The lesion is described as raised or bumpy and fluid-filled. The photo was captured at an angle. Fitzpatrick skin type V. The patient considered this a rash. Reported duration is about one day. The top or side of the foot, back of the hand, arm, sole of the foot and palm are involved. The lesion is associated with enlargement, pain, bothersome appearance and itching:
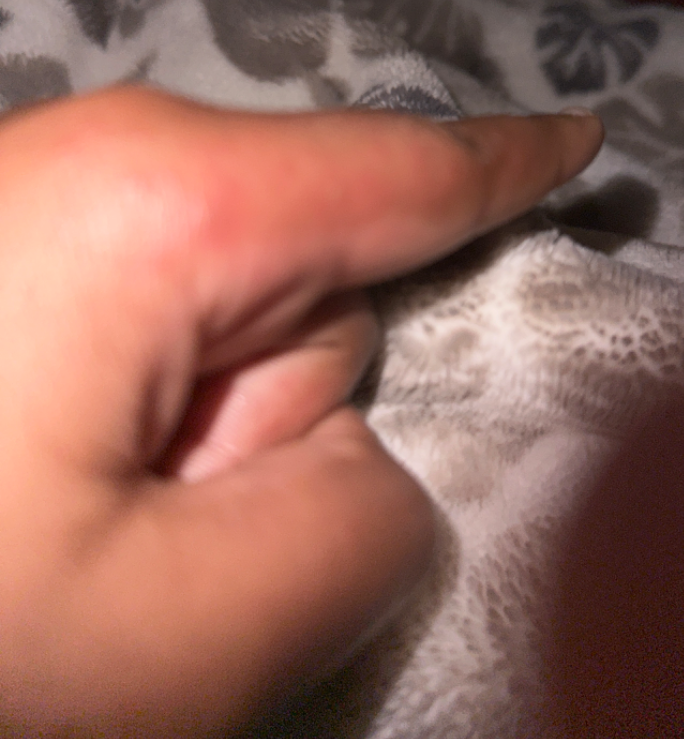assessment — indeterminate